The photograph is a close-up of the affected area.
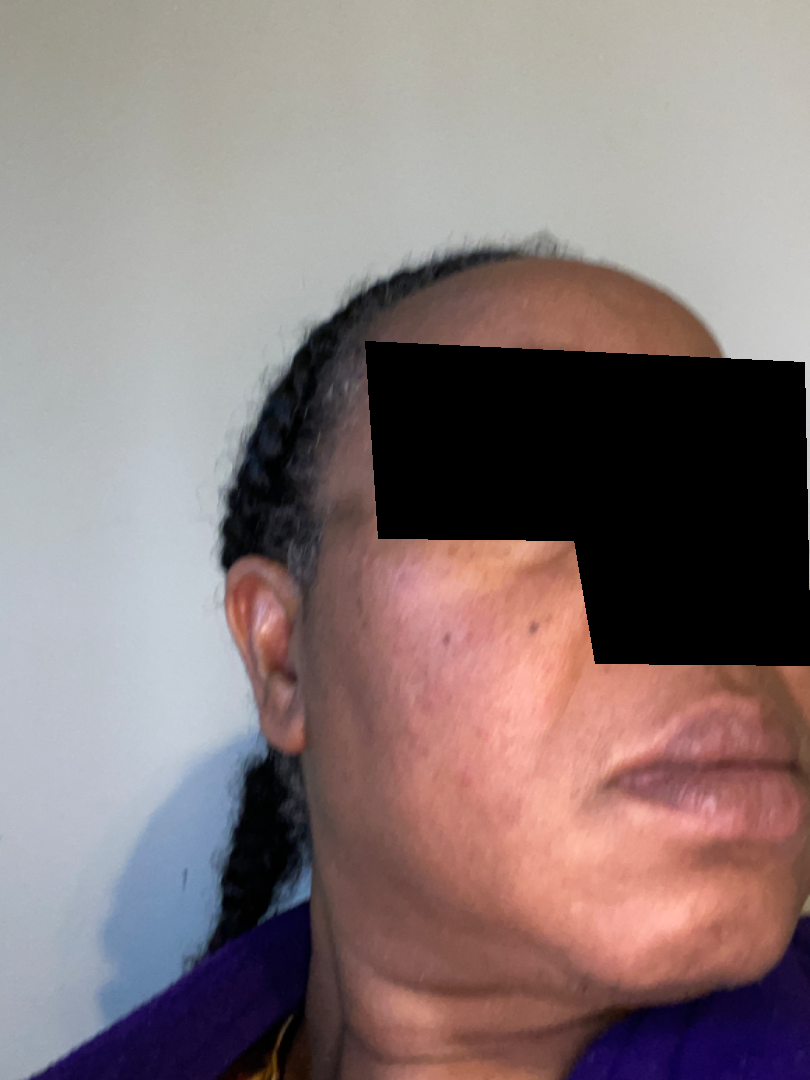The image was not sufficient for the reviewer to characterize the skin condition.
Skin tone: Fitzpatrick V.